The photograph was taken at a distance, Fitzpatrick V.
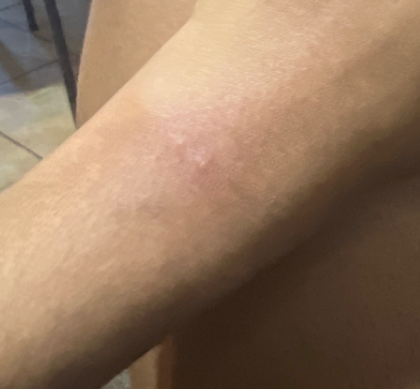Impression:
Allergic Contact Dermatitis (67%); Irritant Contact Dermatitis (33%).